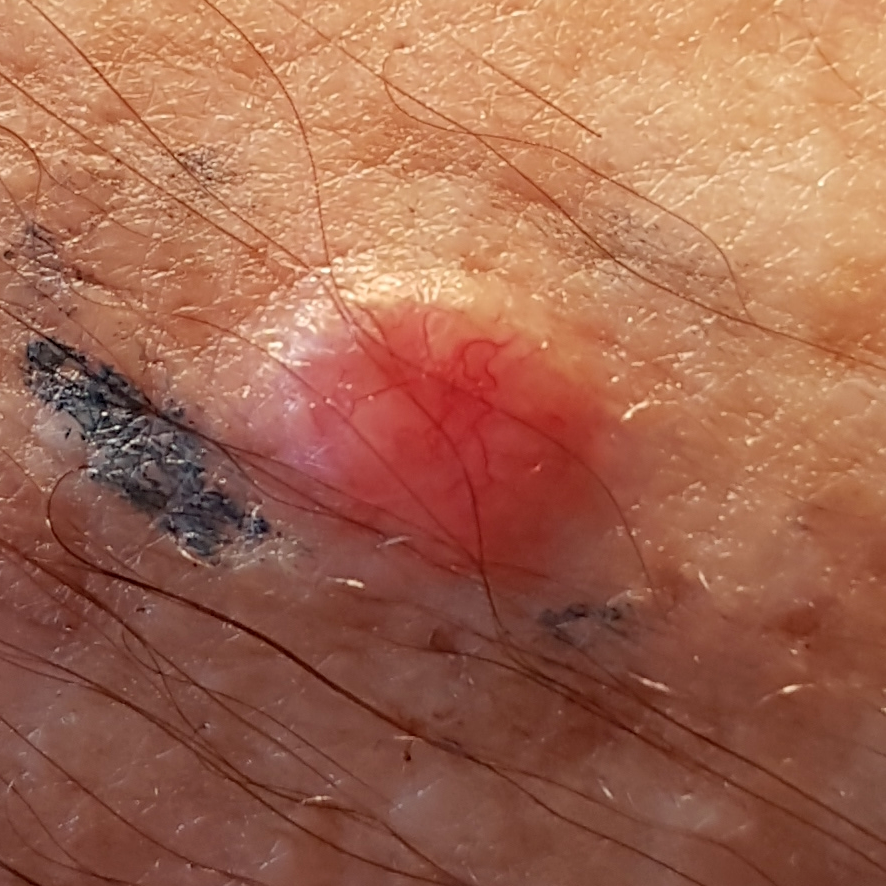Clinical context: A clinical photograph of a skin lesion. A male subject 78 years old. Diagnosis: Histopathologically confirmed as a basal cell carcinoma.